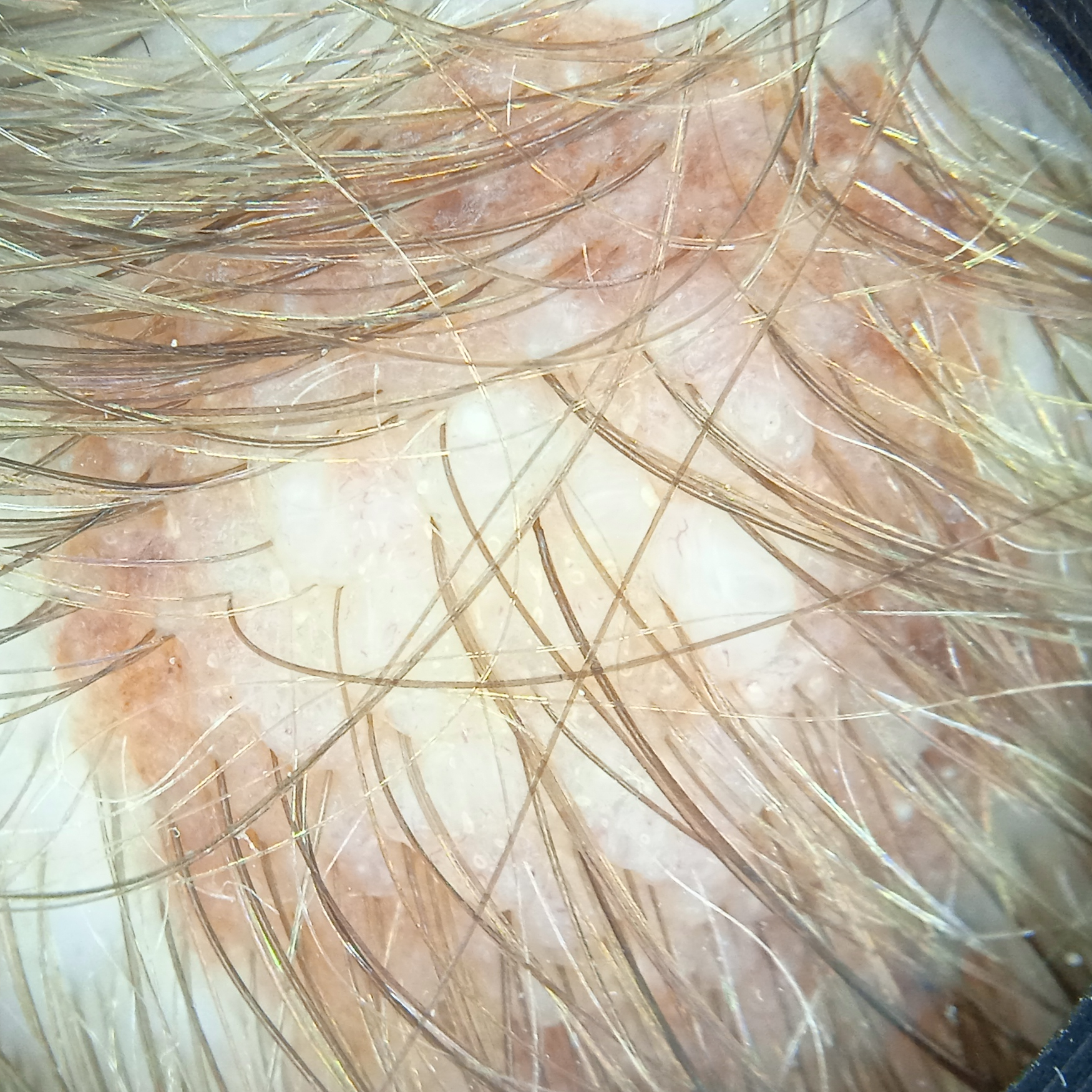<case>
<sun_reaction>skin reddens with sun exposure</sun_reaction>
<mole_burden>few melanocytic nevi overall</mole_burden>
<image>dermoscopic image</image>
<lesion_size>
<diameter_mm>9.1</diameter_mm>
</lesion_size>
<diagnosis>
<name>melanocytic nevus</name>
<malignancy>benign</malignancy>
</diagnosis>
</case>